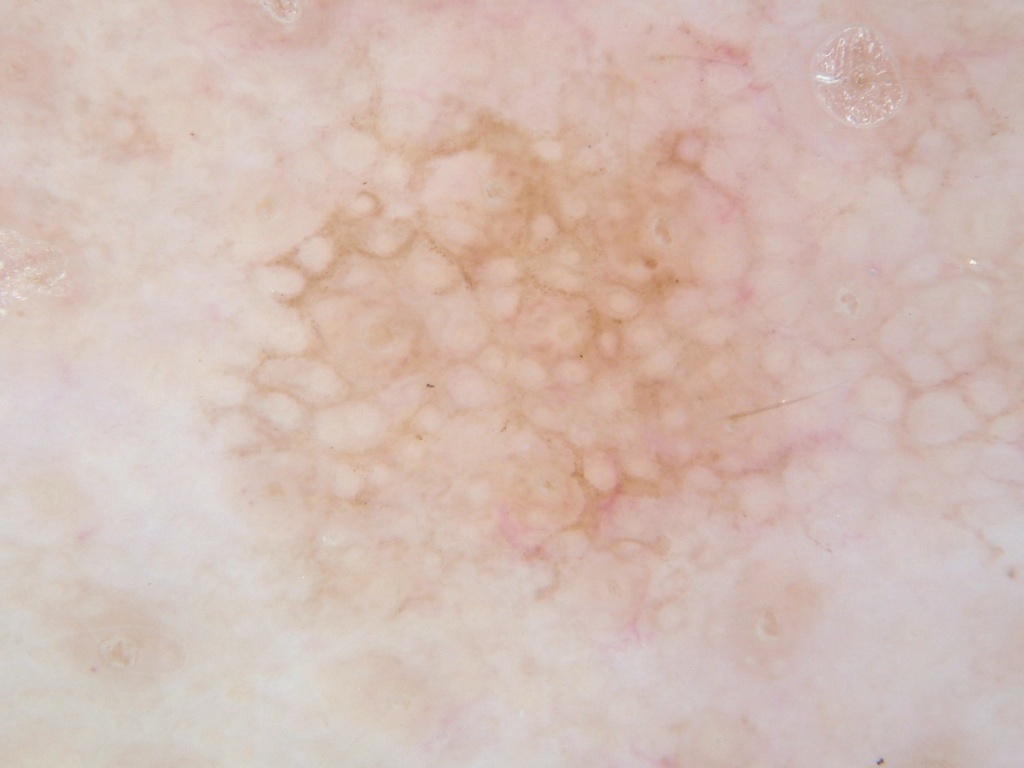A skin lesion imaged with a dermatoscope. In (x1, y1, x2, y2) order, lesion location: box(166, 44, 831, 705). The lesion takes up a large portion of the image. The diagnostic assessment was a benign lesion.